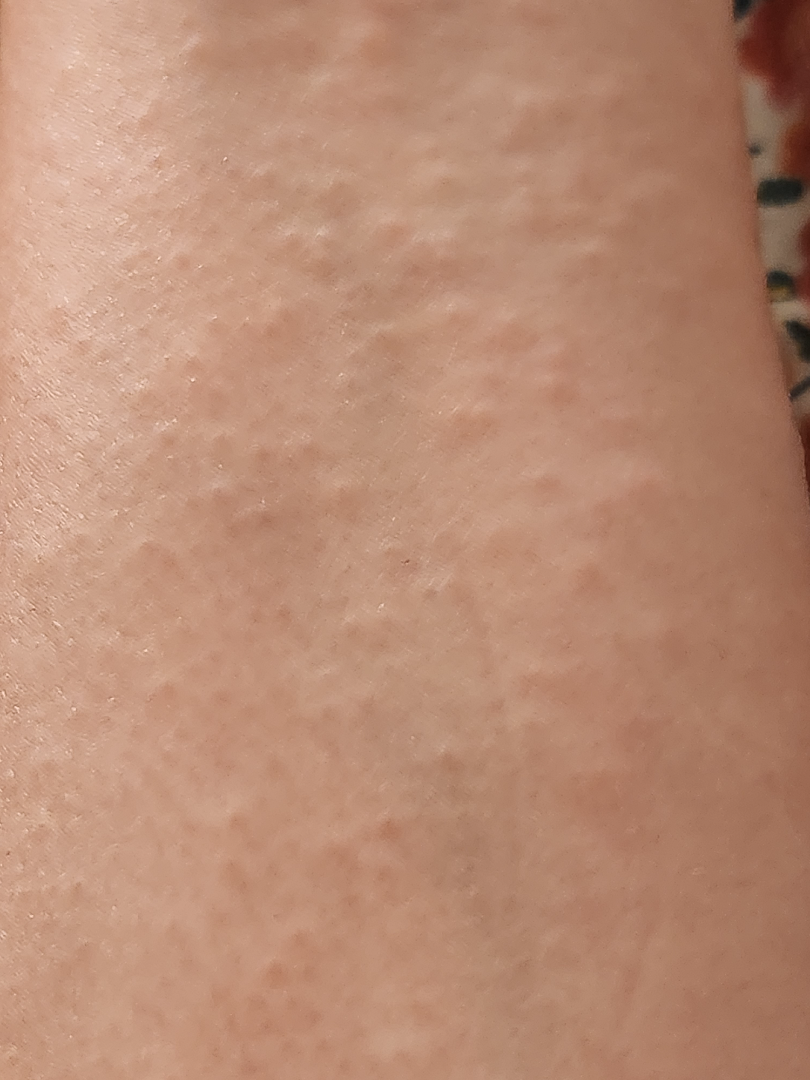The image was not sufficient for the reviewer to characterize the skin condition. Reported duration is less than one week. No associated systemic symptoms reported. Close-up view. The patient reports itching. Located on the arm. The patient considered this a rash.